A dermoscopic close-up of a skin lesion.
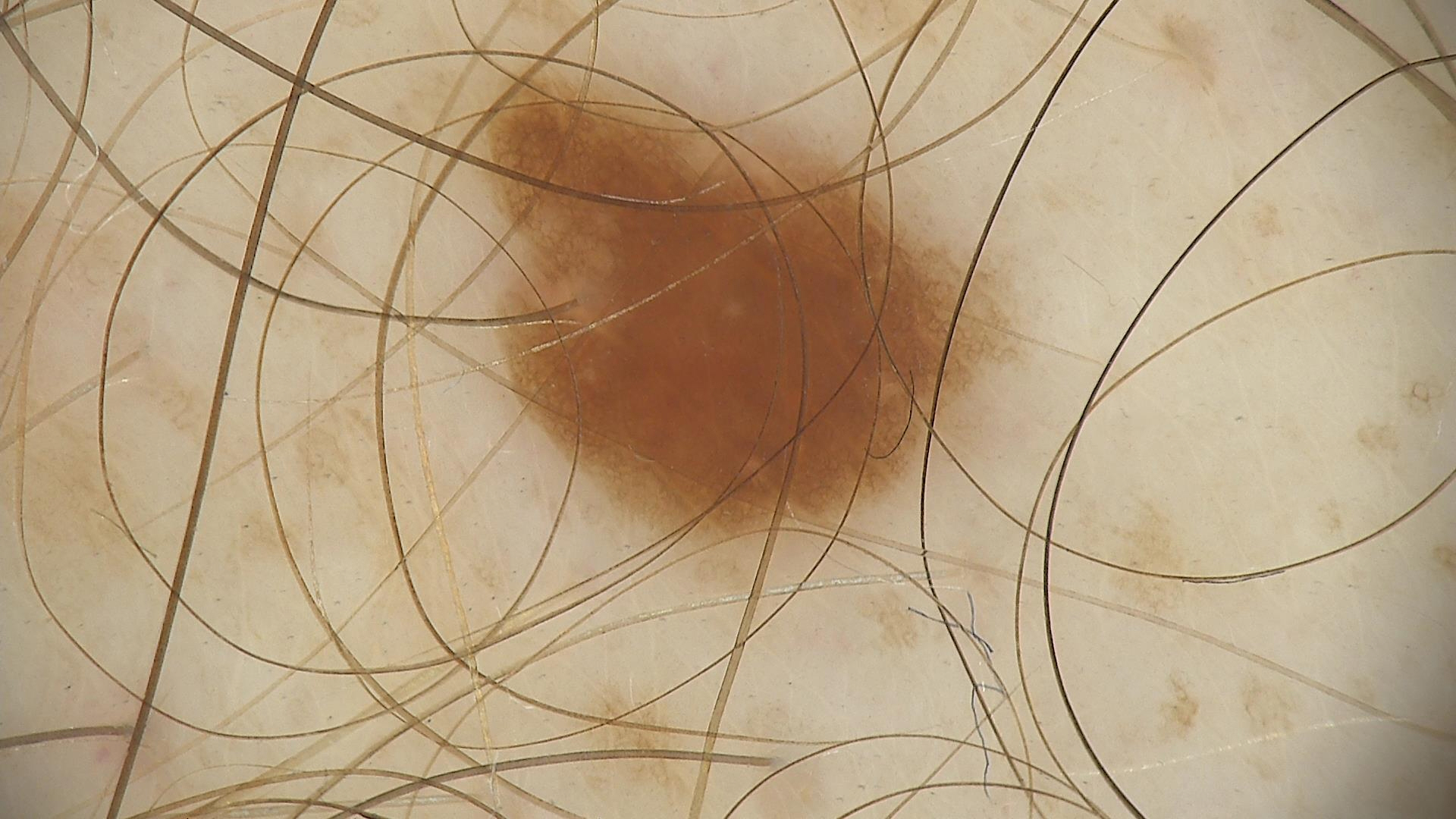Impression: The diagnosis was a benign lesion — a dysplastic junctional nevus.